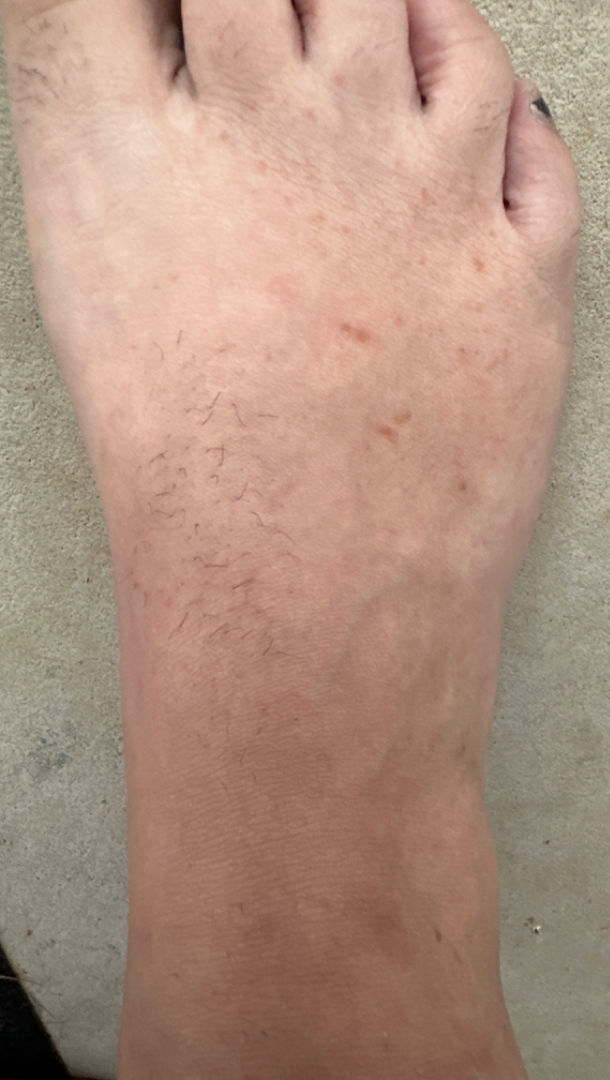| key | value |
|---|---|
| assessment | not assessable |